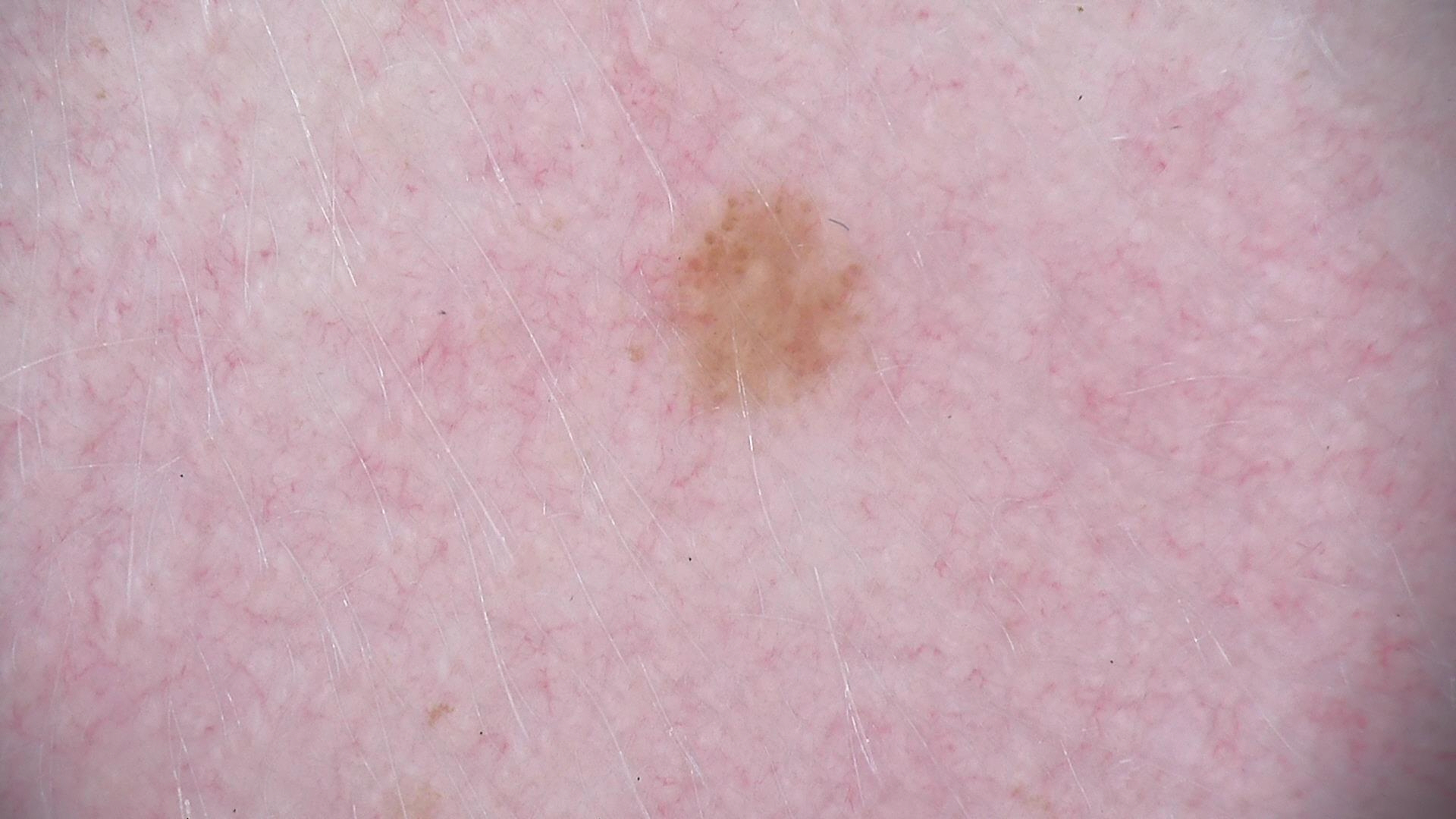Dermoscopy of a skin lesion.
Labeled as a benign lesion — a dysplastic junctional nevus.